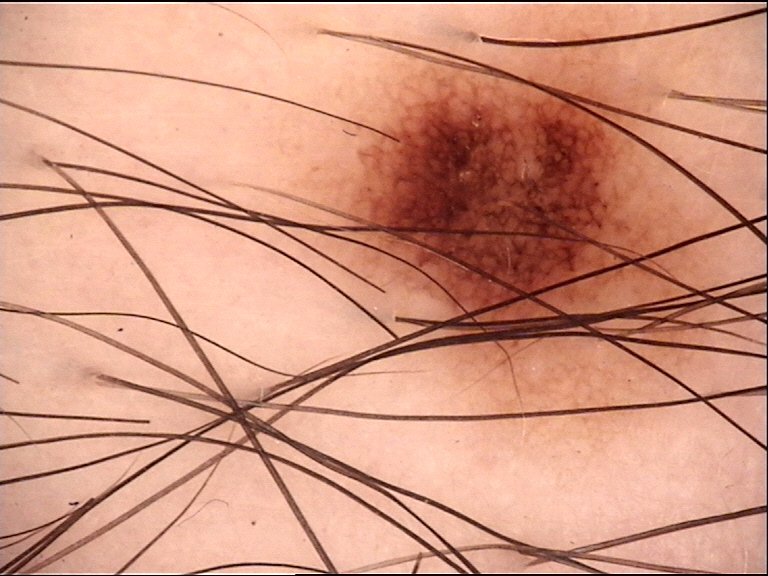{"image": "dermatoscopy", "diagnosis": {"name": "dysplastic junctional nevus", "code": "jd", "malignancy": "benign", "super_class": "melanocytic", "confirmation": "expert consensus"}}